A male patient 72 years old. Few moles overall by the patient's own estimate. By self-report, a personal history of cancer, no immunosuppression, and no prior organ transplant: 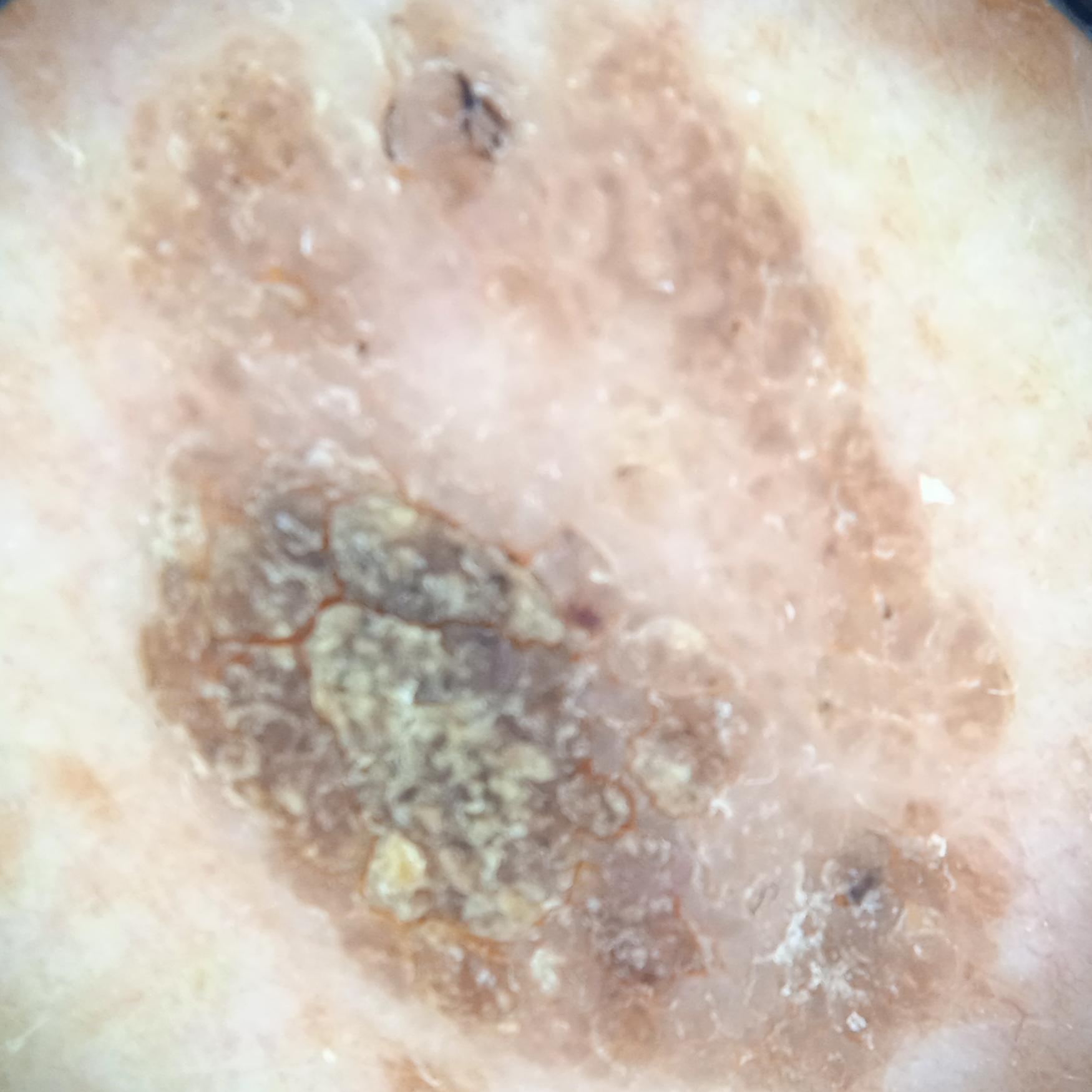Summary:
The lesion is on the back.
Impression:
The lesion was assessed as a seborrheic keratosis.